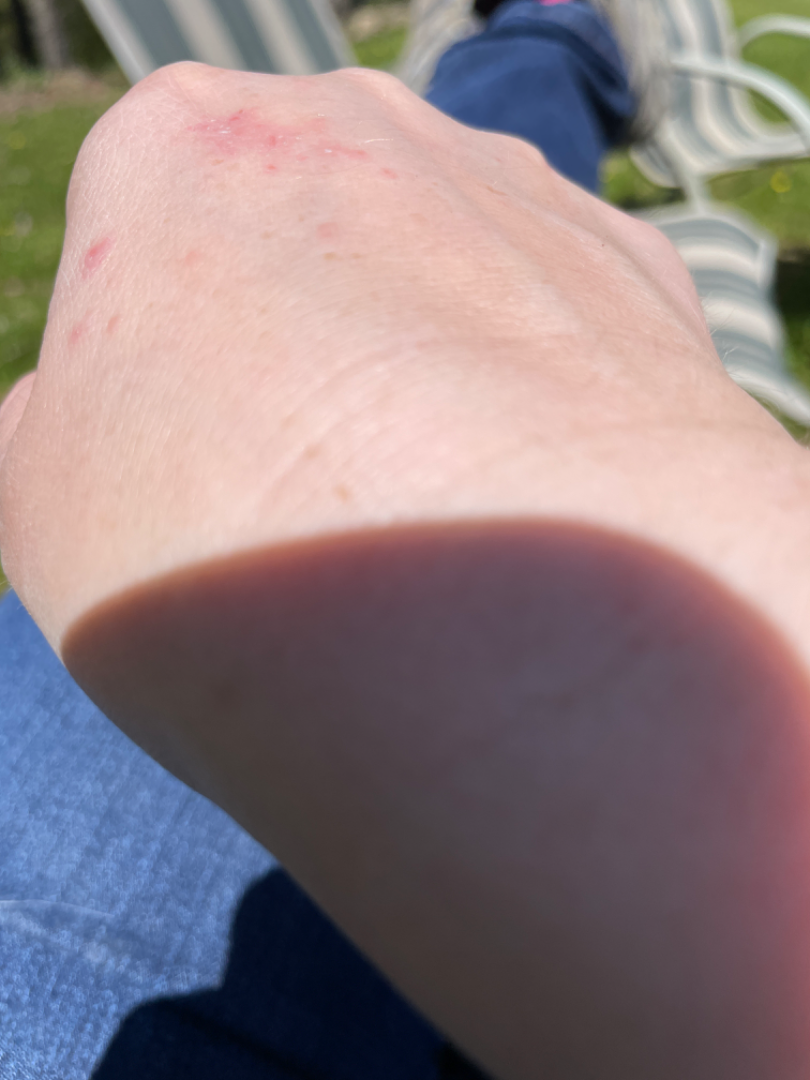| feature | finding |
|---|---|
| shot type | at an angle |
| self-categorized as | a rash |
| lesion texture | raised or bumpy |
| location | back of the hand |
| symptom duration | one to four weeks |
| lesion symptoms | itching, enlargement and bothersome appearance |
| other reported symptoms | fatigue and mouth sores |
| dermatologist impression | most consistent with Irritant Contact Dermatitis; with consideration of Allergic Contact Dermatitis |